A dermoscopy image of a single skin lesion.
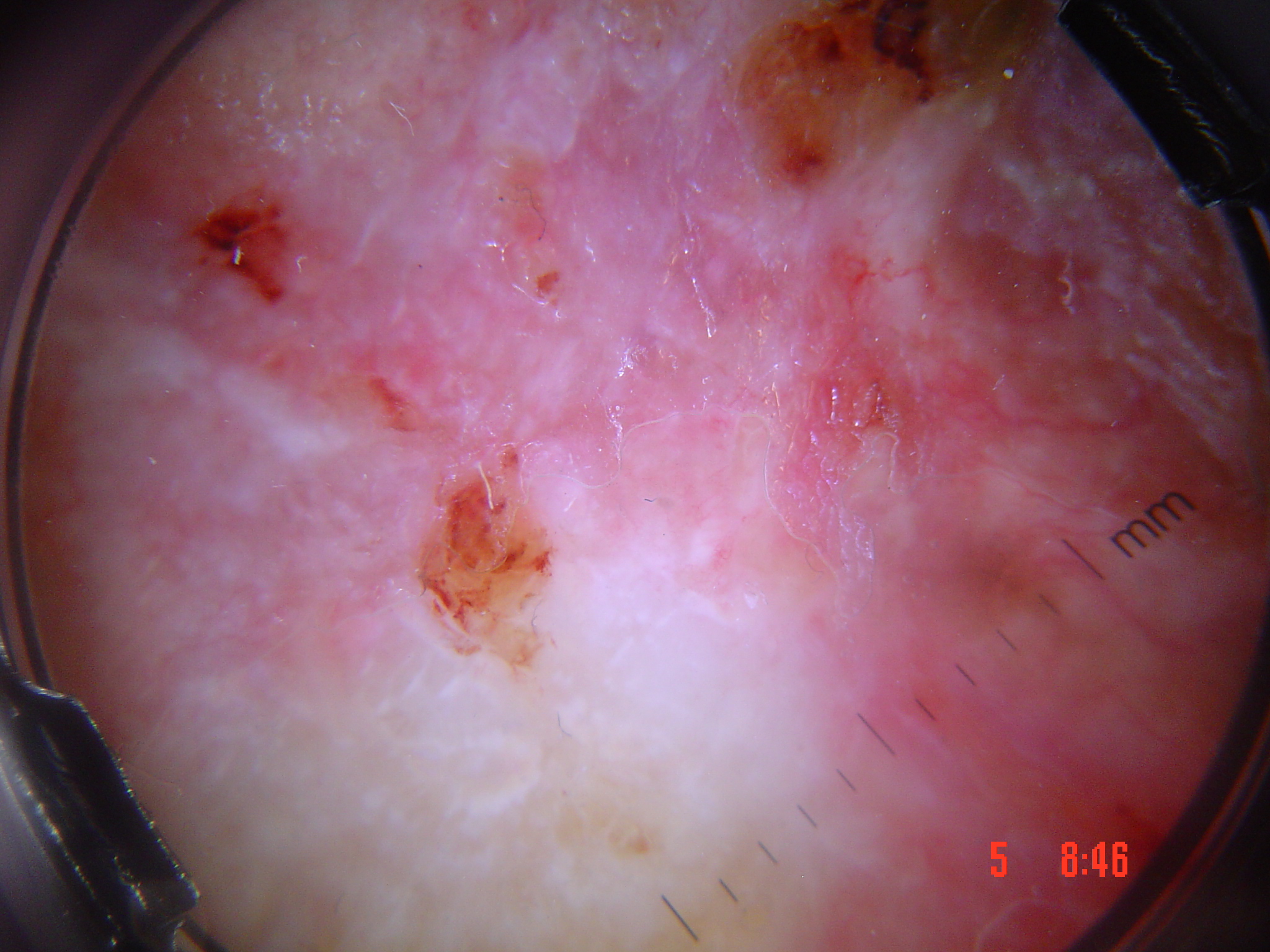Case:
• class — squamous cell carcinoma (biopsy-proven)